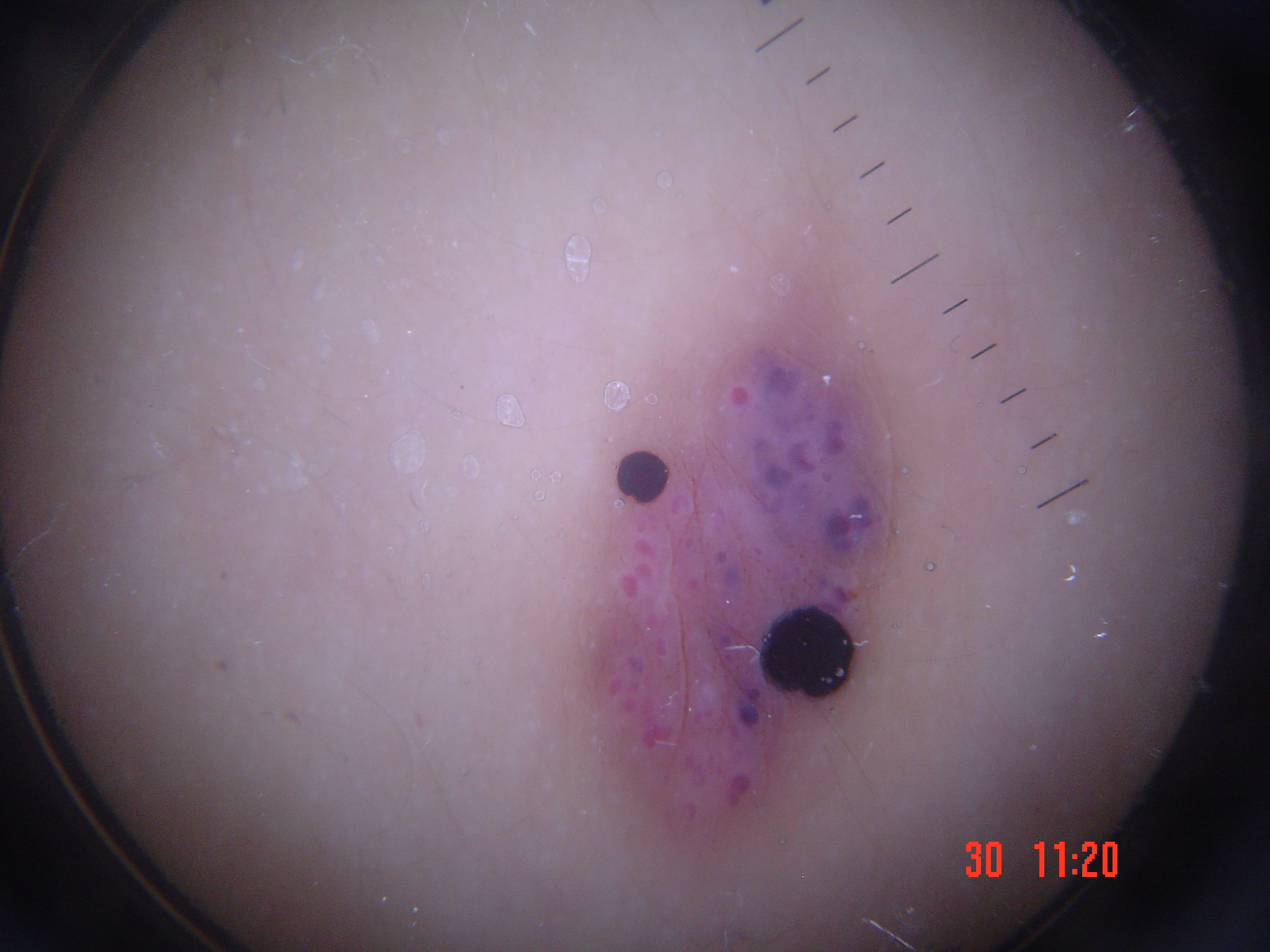Case: A dermoscopic image of a skin lesion. Conclusion: Diagnosed as a vascular lesion — an angiokeratoma.